An image taken at an angle:
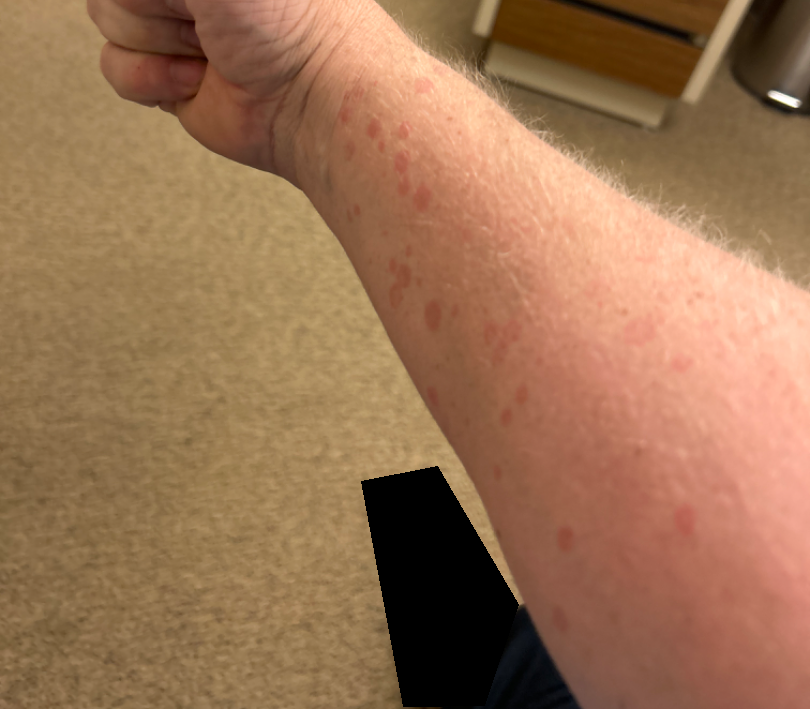Tinea Versicolor (leading).